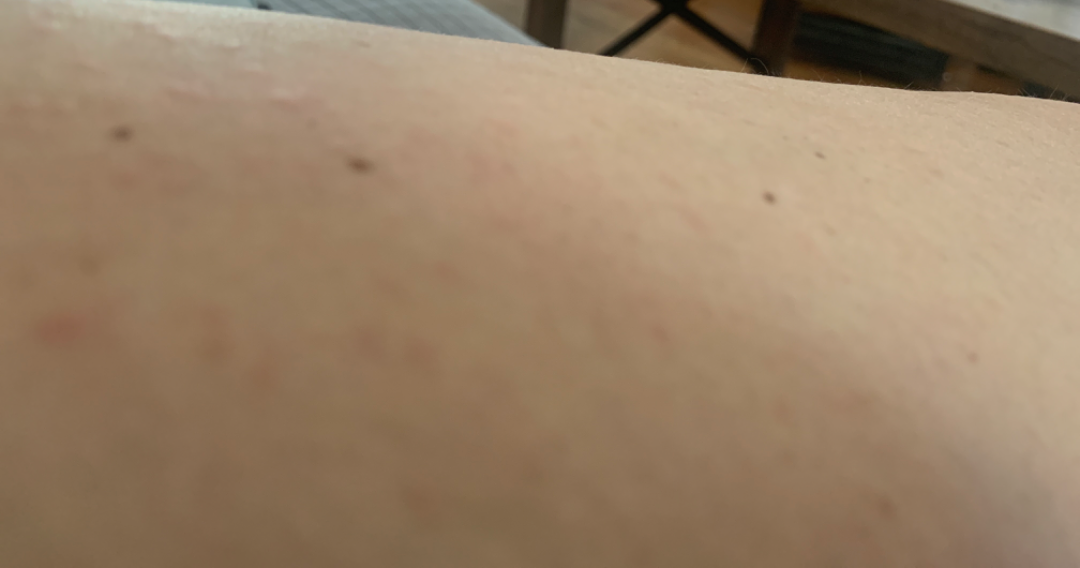The skin findings could not be characterized from the image. The lesion is associated with itching. An image taken at an angle. Fitzpatrick III. Reported duration is about one day. The lesion involves the front of the torso, back of the torso and leg. Texture is reported as raised or bumpy. No associated systemic symptoms reported.